Dermoscopy of a skin lesion · a male patient approximately 40 years of age:
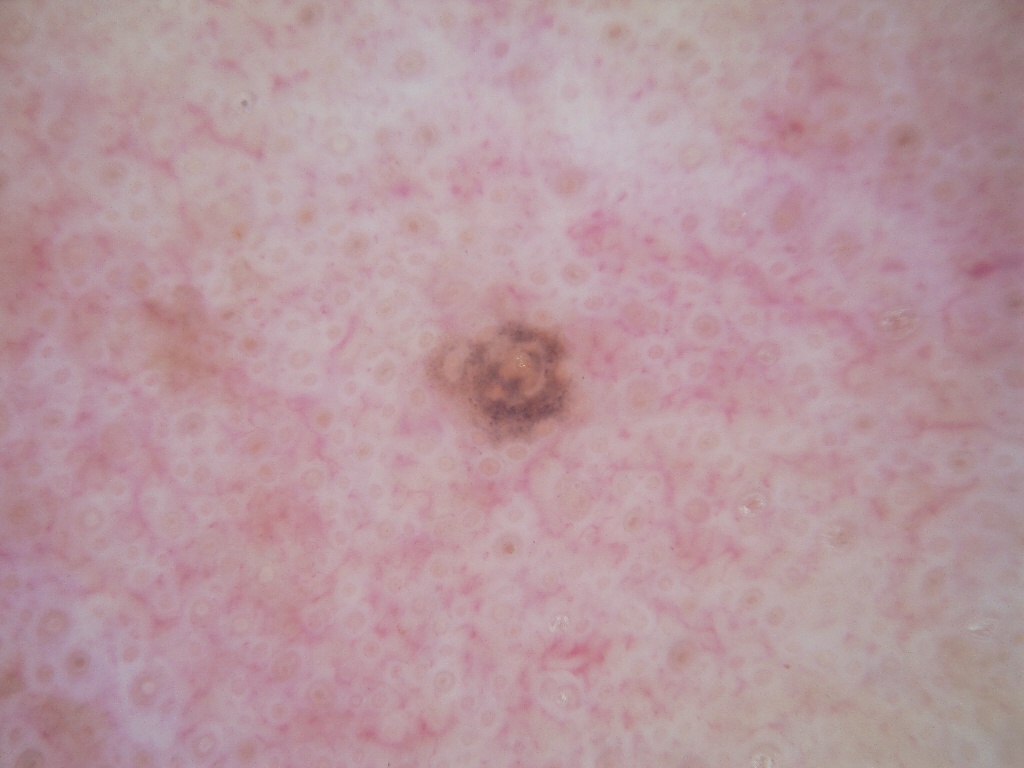• lesion bbox · (424, 310, 581, 446)
• absent dermoscopic features · milia-like cysts, negative network, pigment network, streaks, and globules
• size · small
• assessment · a melanocytic nevus